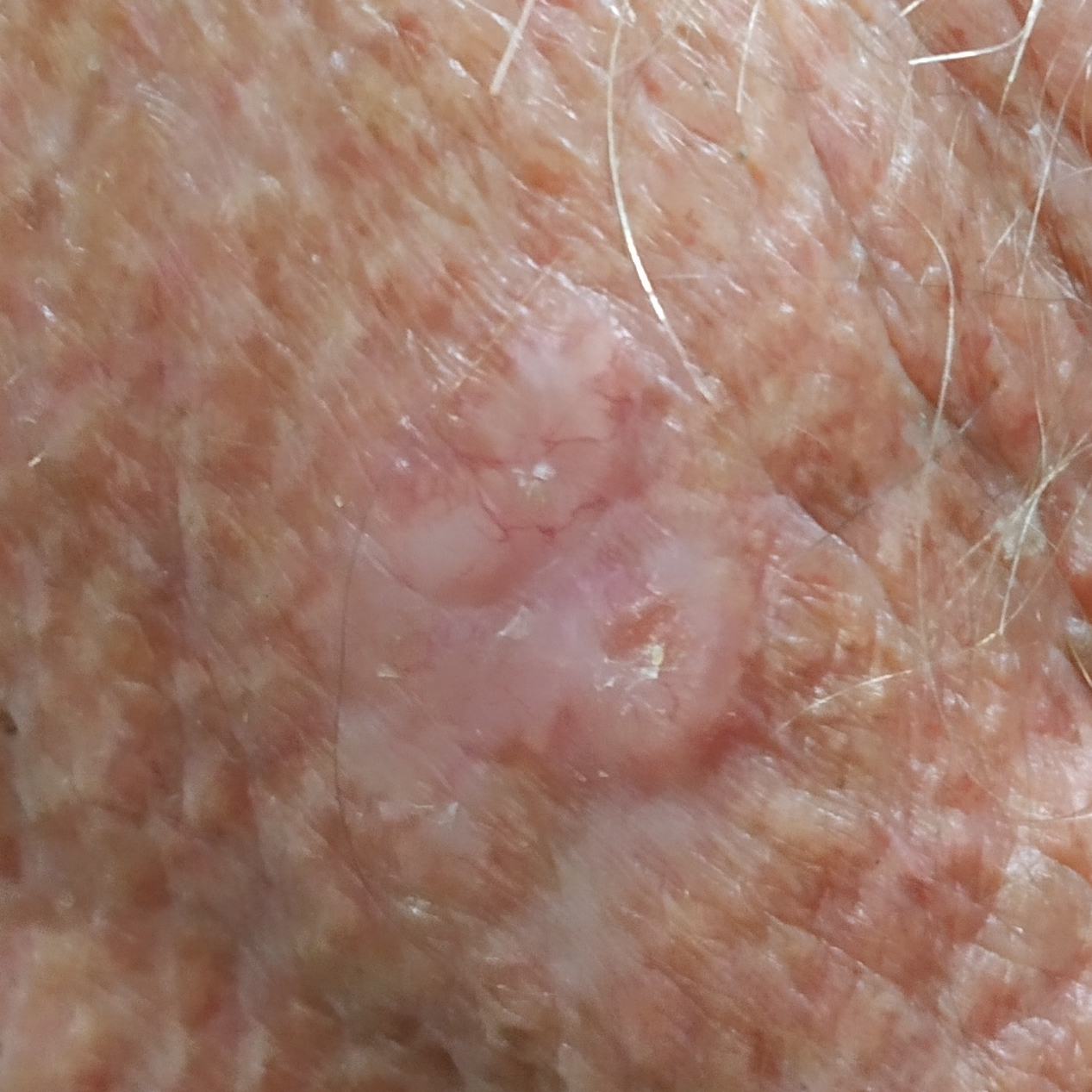image = clinical photo | risk factors = prior skin cancer (patient or family), pesticide exposure | subject = male, in their 70s | skin type = II | anatomic site = the neck | lesion size = 14 × 11 mm | symptoms = elevation, itching | pathology = basal cell carcinoma (biopsy-proven).